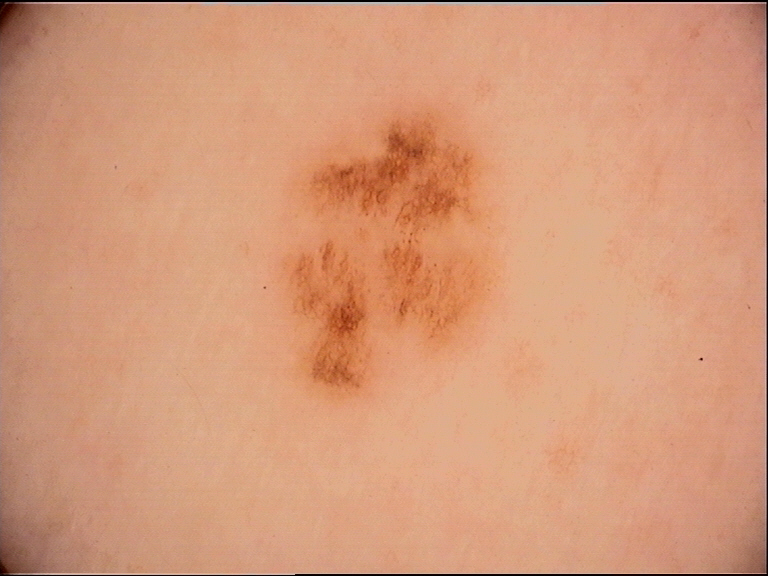Labeled as a dysplastic junctional nevus.